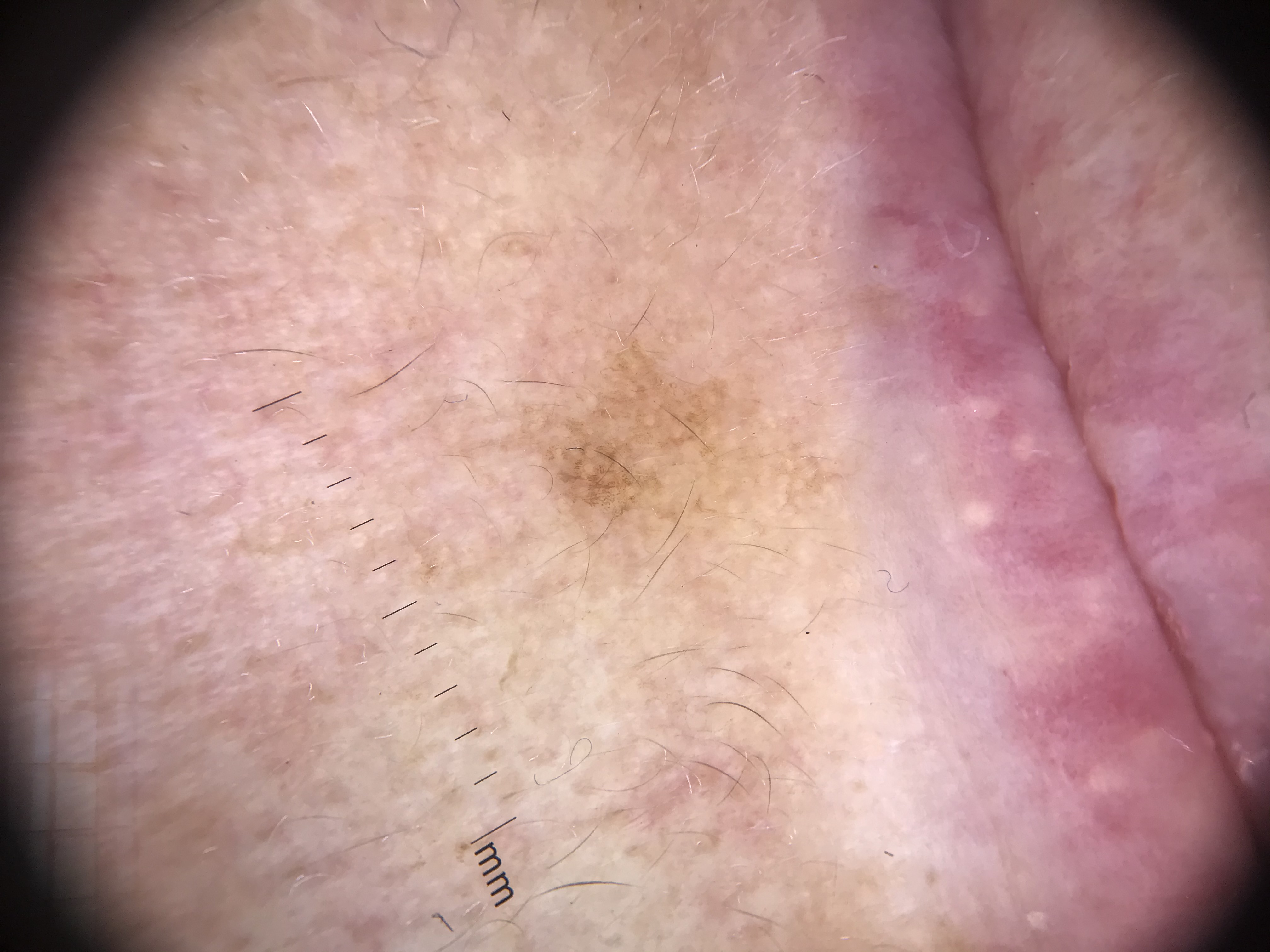imaging — dermatoscopy; class — solar lentigo (expert consensus).